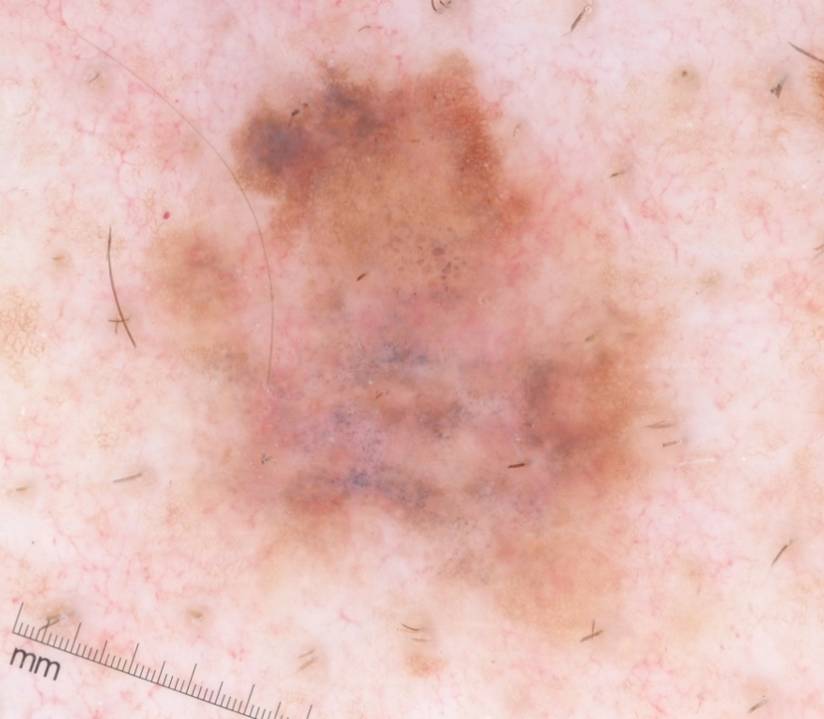{
  "image": {
    "modality": "dermoscopy"
  },
  "dermoscopic_features": {
    "present": [
      "globules",
      "pigment network"
    ],
    "absent": [
      "milia-like cysts",
      "streaks",
      "negative network"
    ]
  },
  "lesion_location": {
    "bbox_xyxy": [
      145,
      50,
      674,
      634
    ]
  },
  "lesion_extent": {
    "approx_field_fraction_pct": 33
  },
  "diagnosis": {
    "name": "melanoma",
    "malignancy": "malignant",
    "lineage": "melanocytic",
    "provenance": "histopathology"
  }
}